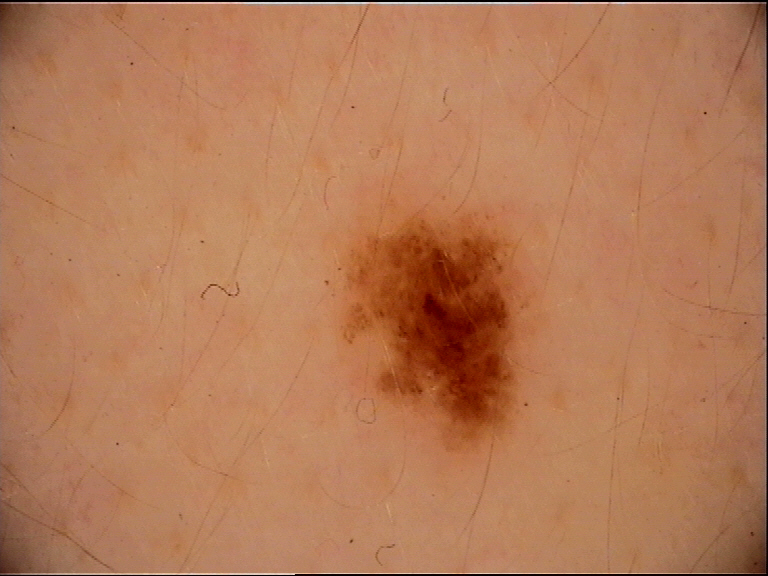Classified as a dysplastic junctional nevus.